A female subject aged 53-57 · a skin lesion imaged with contact-polarized dermoscopy:
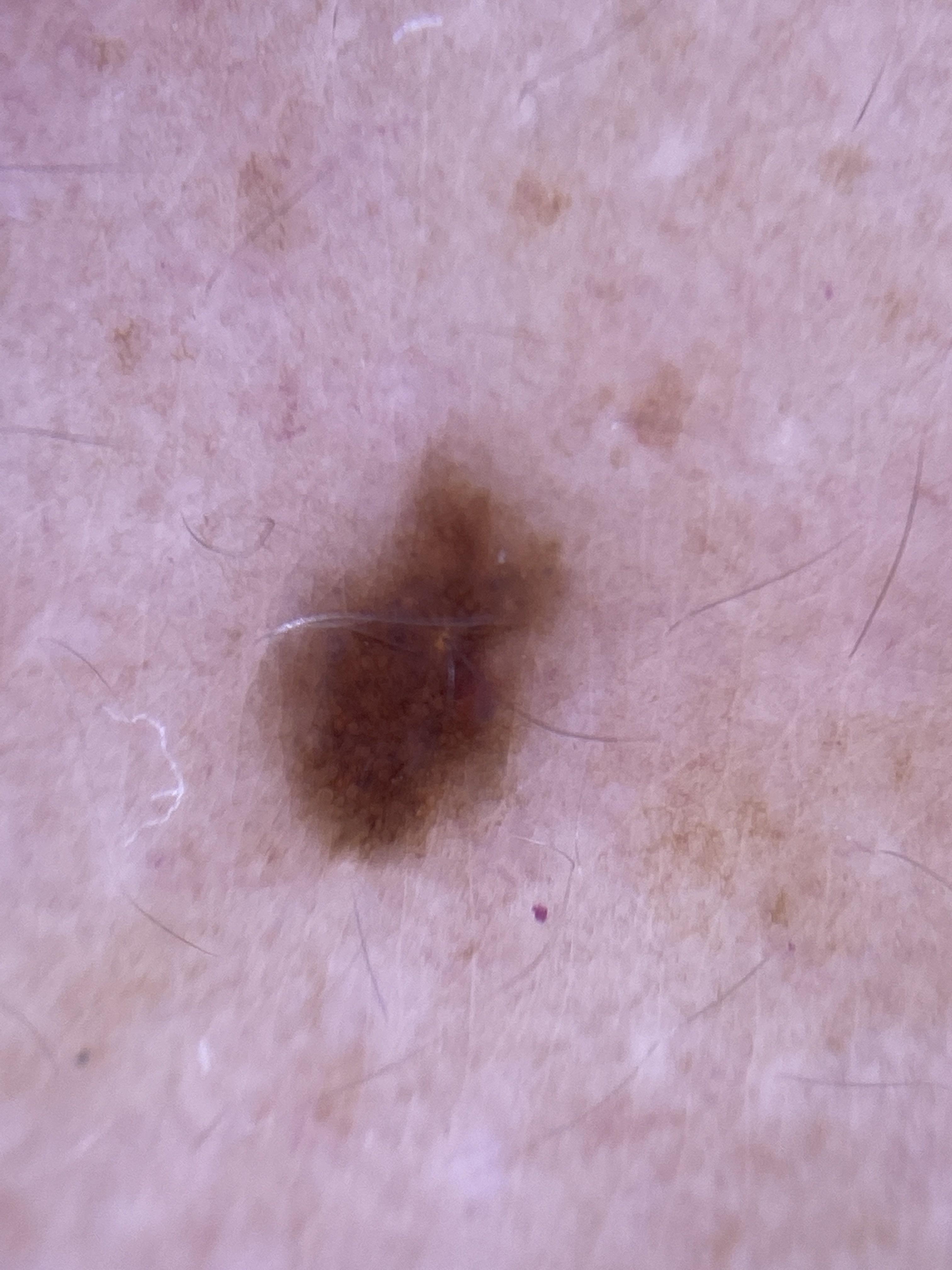Case:
- site — the trunk (the anterior trunk)
- assessment — Nevus